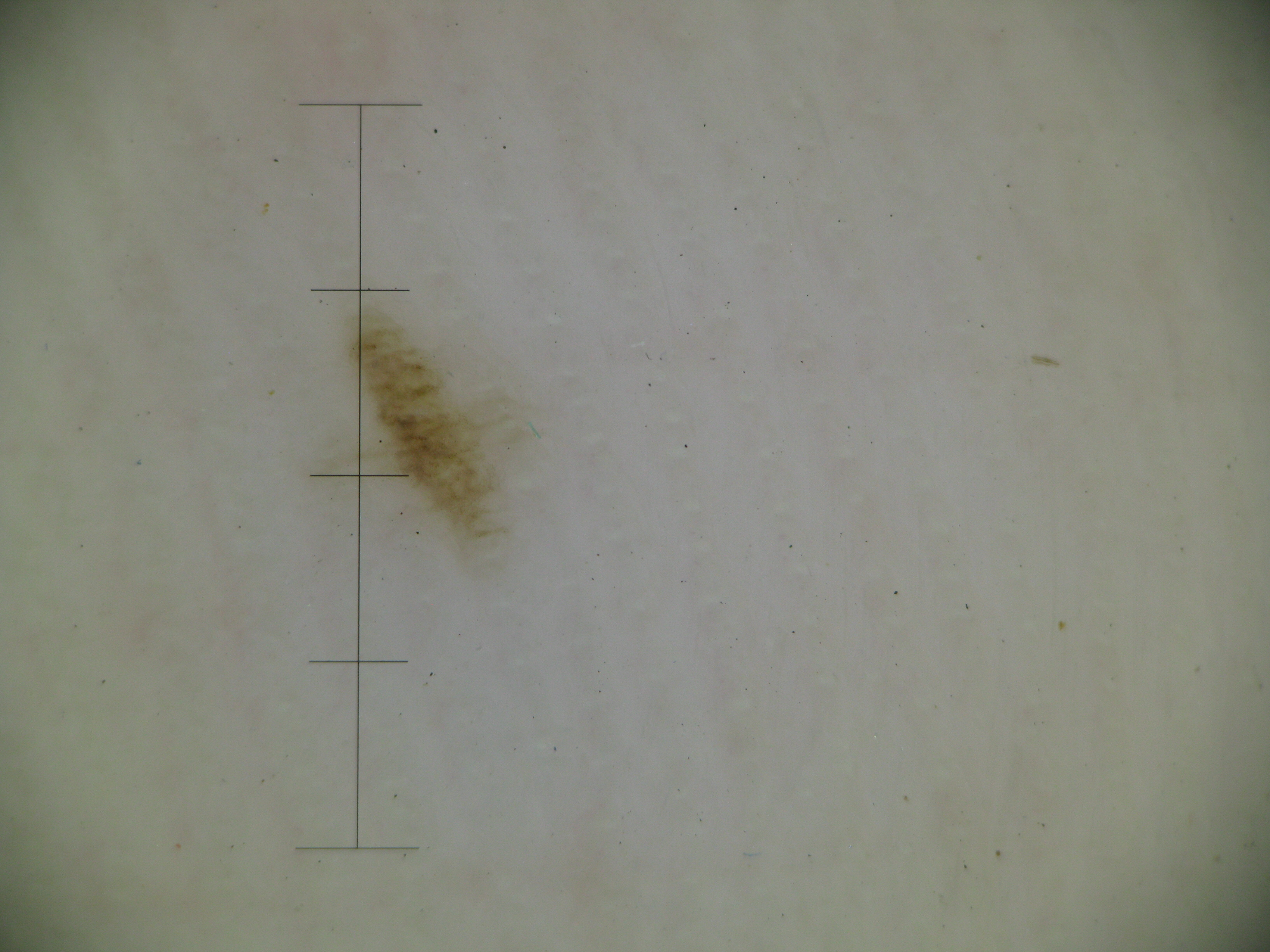Case:
- label — acral junctional nevus (expert consensus)